A dermatoscopic image of a skin lesion:
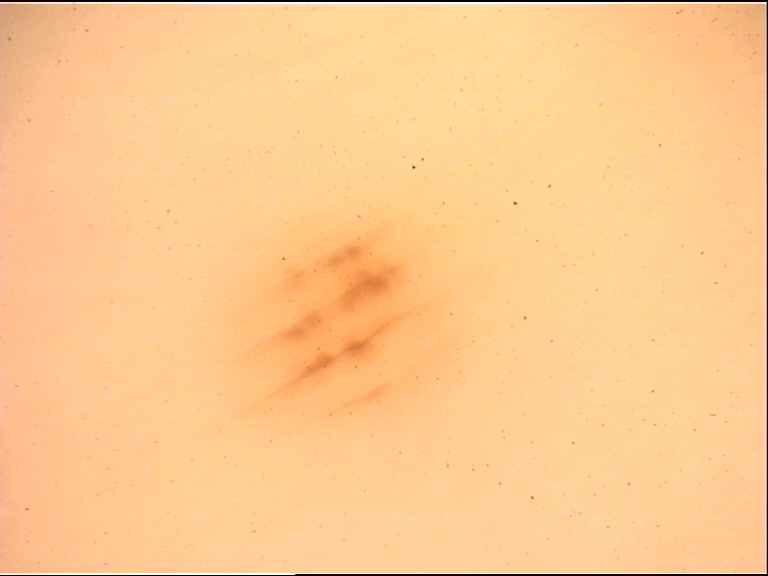diagnosis = acral junctional nevus (expert consensus).